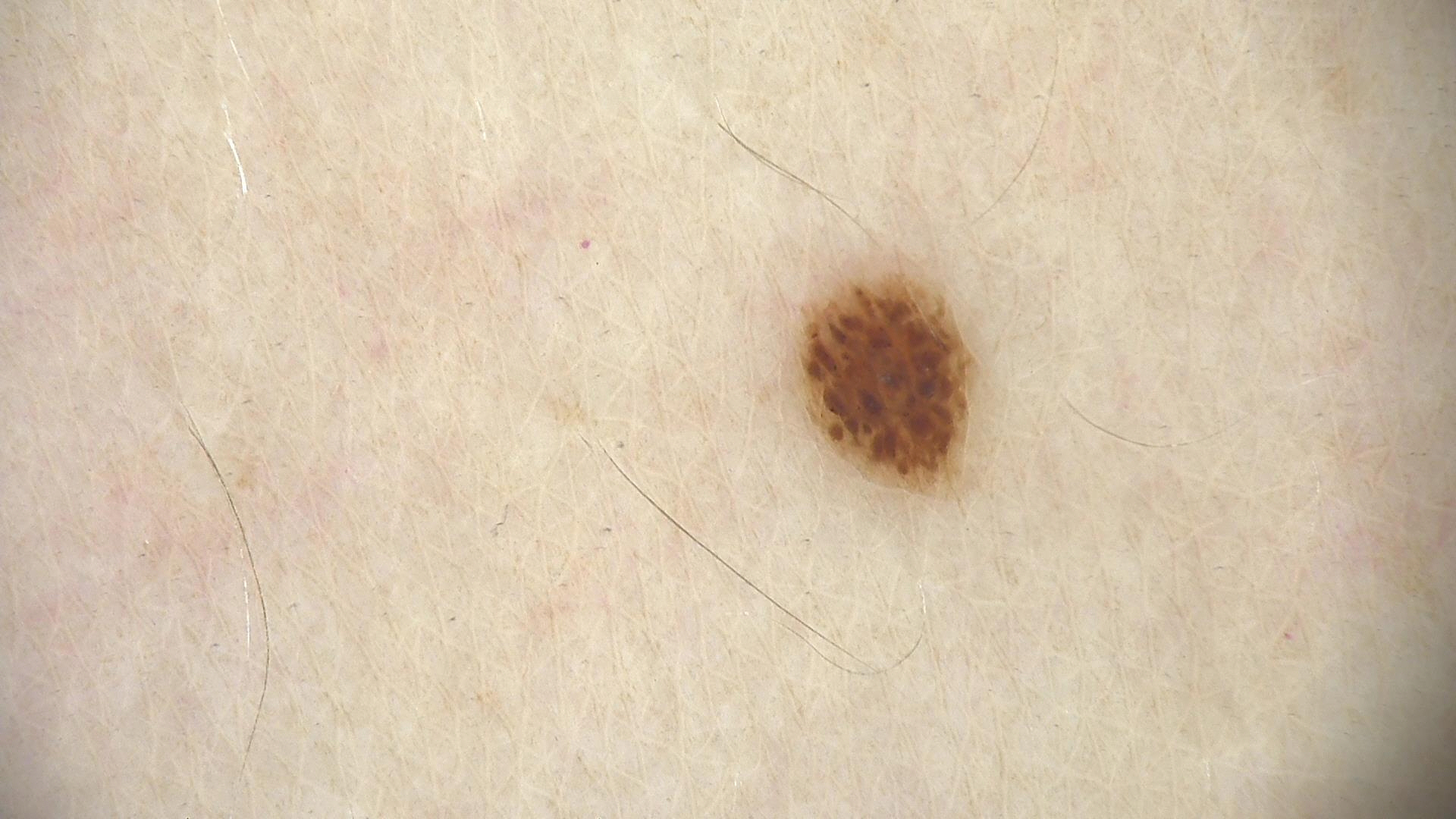Findings:
A dermoscopic image of a skin lesion.
Impression:
Classified as a dysplastic junctional nevus.